Imaged for a research study, with no referral diagnosis recorded; a clinical close-up of a skin lesion: 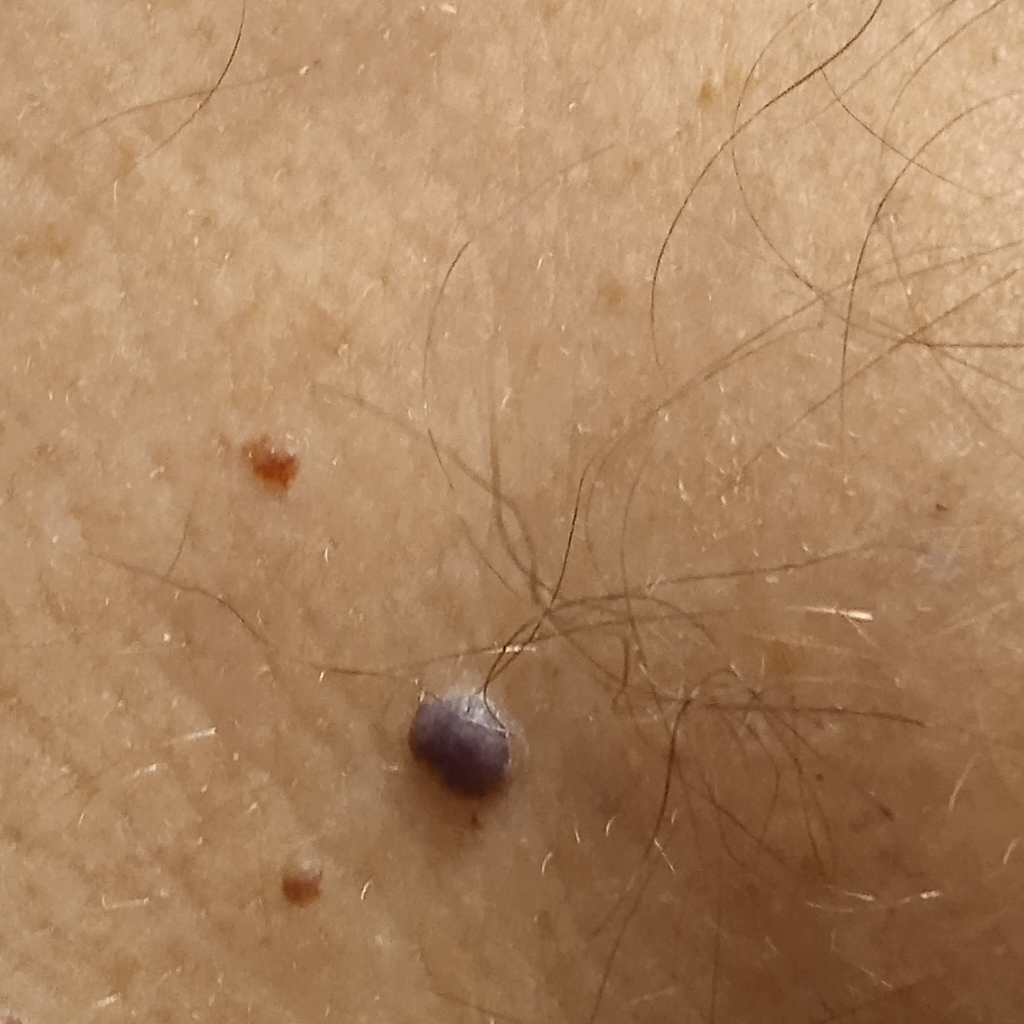The lesion is about 4.7 mm across. The diagnostic impression was an angioma.